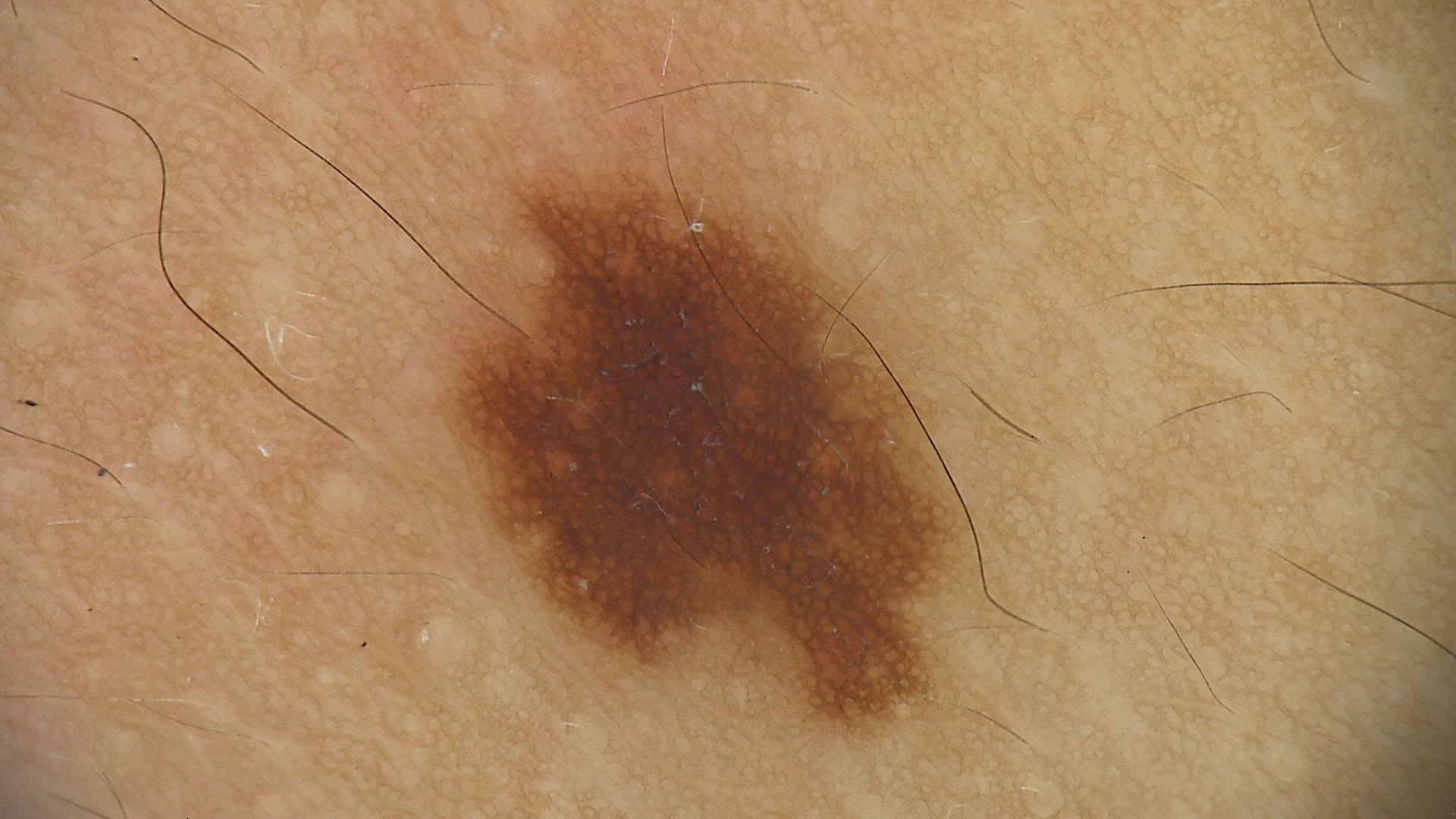class=dysplastic junctional nevus (expert consensus)